The affected area is the arm; an image taken at an angle; the contributor is 30–39, female.
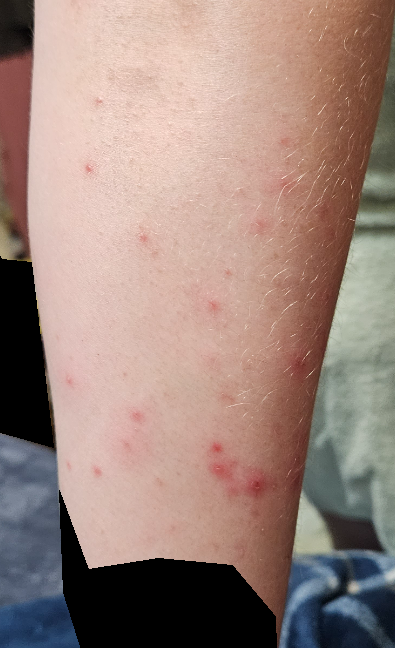<summary>
<symptoms>bothersome appearance, itching</symptoms>
<patient_category>a rash</patient_category>
<duration>one to four weeks</duration>
<texture>fluid-filled, raised or bumpy</texture>
<differential>
  <tied_lead>Folliculitis, Herpes Simplex</tied_lead>
  <considered>Contact dermatitis</considered>
</differential>
</summary>